The photo was captured at a distance — 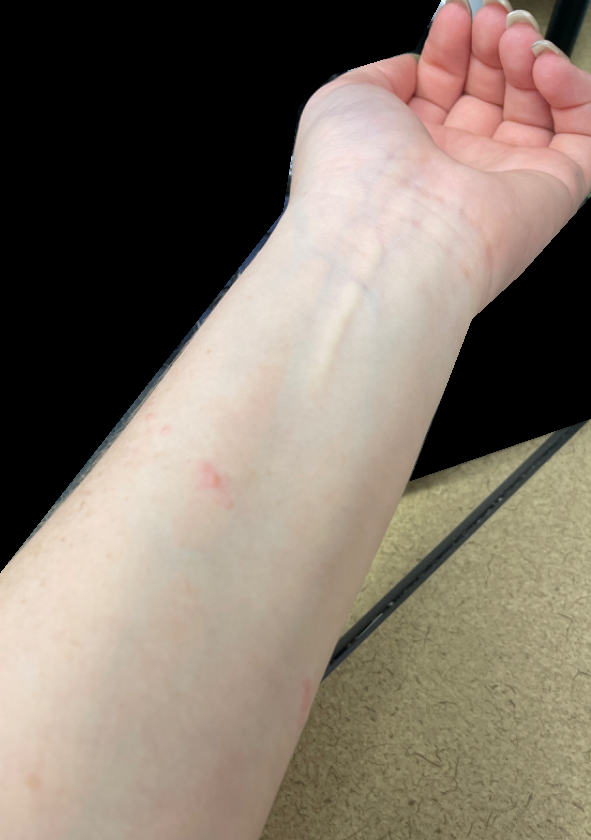| key | value |
|---|---|
| assessment | indeterminate from the photograph |